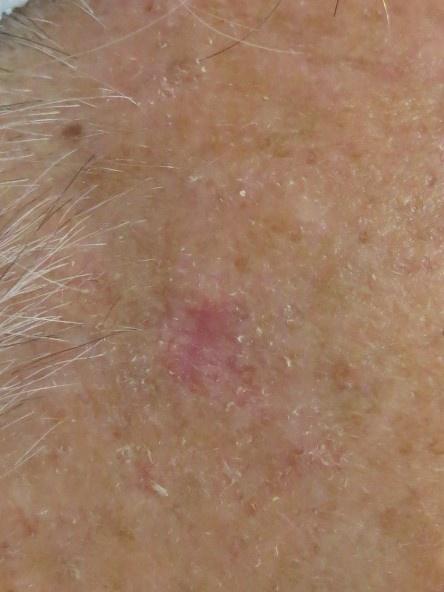A male patient aged approximately 80.
Histopathologically confirmed as a malignant, adnexal lesion — a basal cell carcinoma.